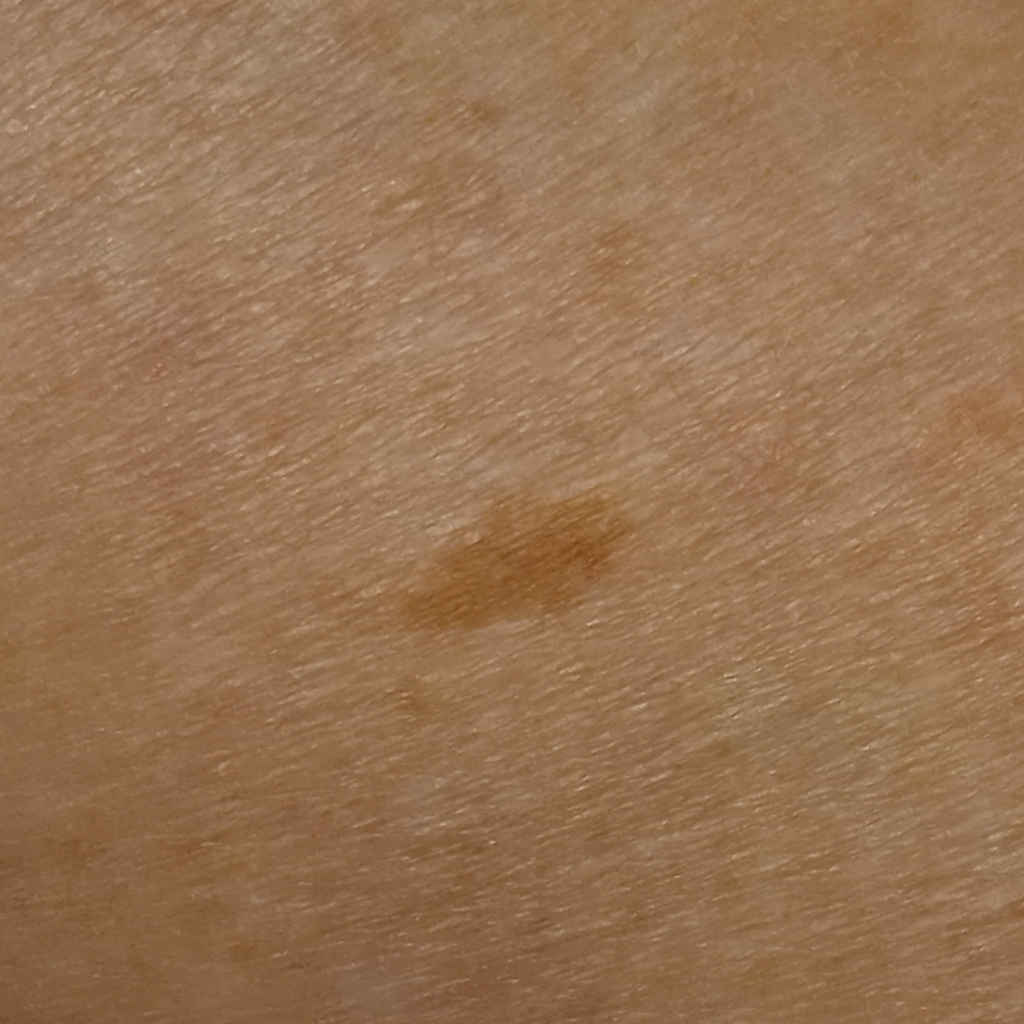Case:
– modality · clinical photo
– referral context · research study (no referral diagnosis)
– subject · female, 75 years of age
– size · 8.2 mm
– diagnosis · melanocytic nevus (dermatologist consensus)